The patient described the issue as skin that appeared healthy to them · the affected area is the arm and front of the torso · the lesion is described as raised or bumpy · the lesion is associated with itching and enlargement · present for one to four weeks · the photo was captured at an angle · female subject, age 50–59 · the patient notes associated fatigue and shortness of breath: 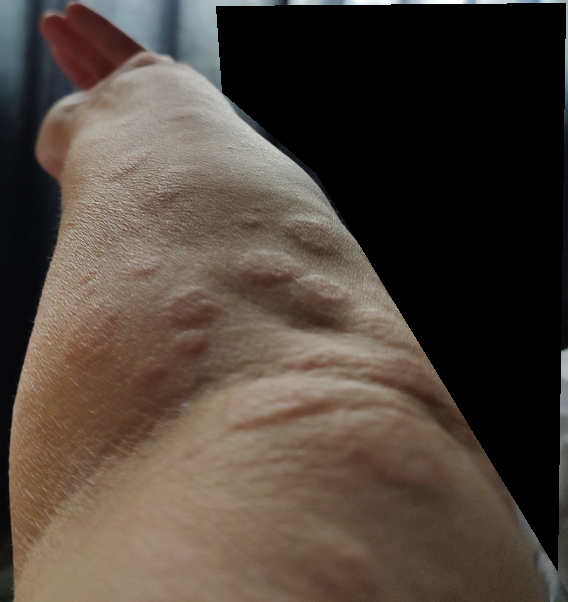On remote review of the image, Cutaneous metastasis (0.54); Urticaria (0.23); Pseudolymphoma (0.23).